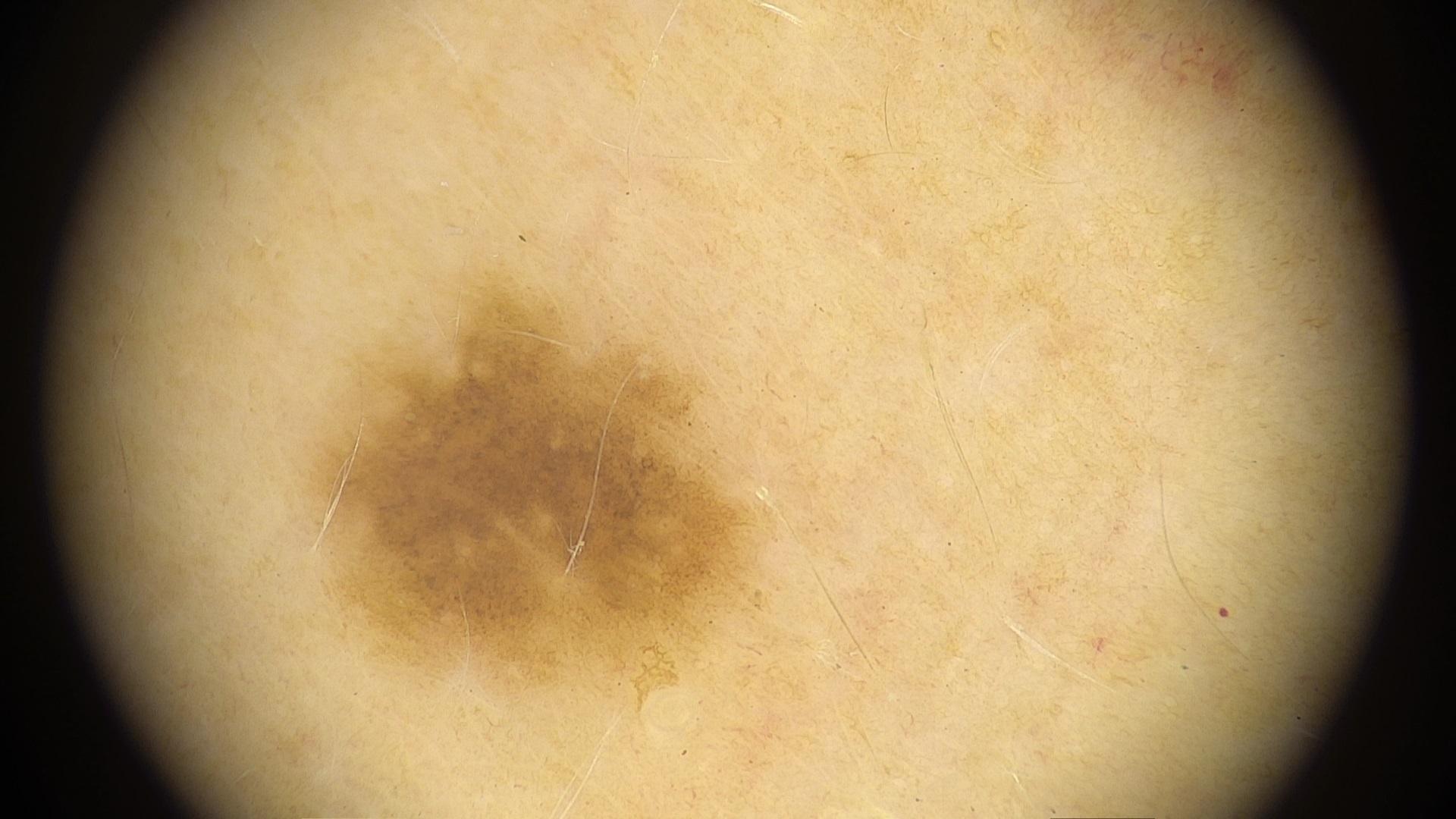modality = dermoscopy | skin type = II | risk factors = no melanoma in first-degree relatives and no previous melanoma | subject = female, in their mid- to late 30s | body site = the trunk | diagnostic label = Nevus (clinical impression).